Dermoscopy of a skin lesion.
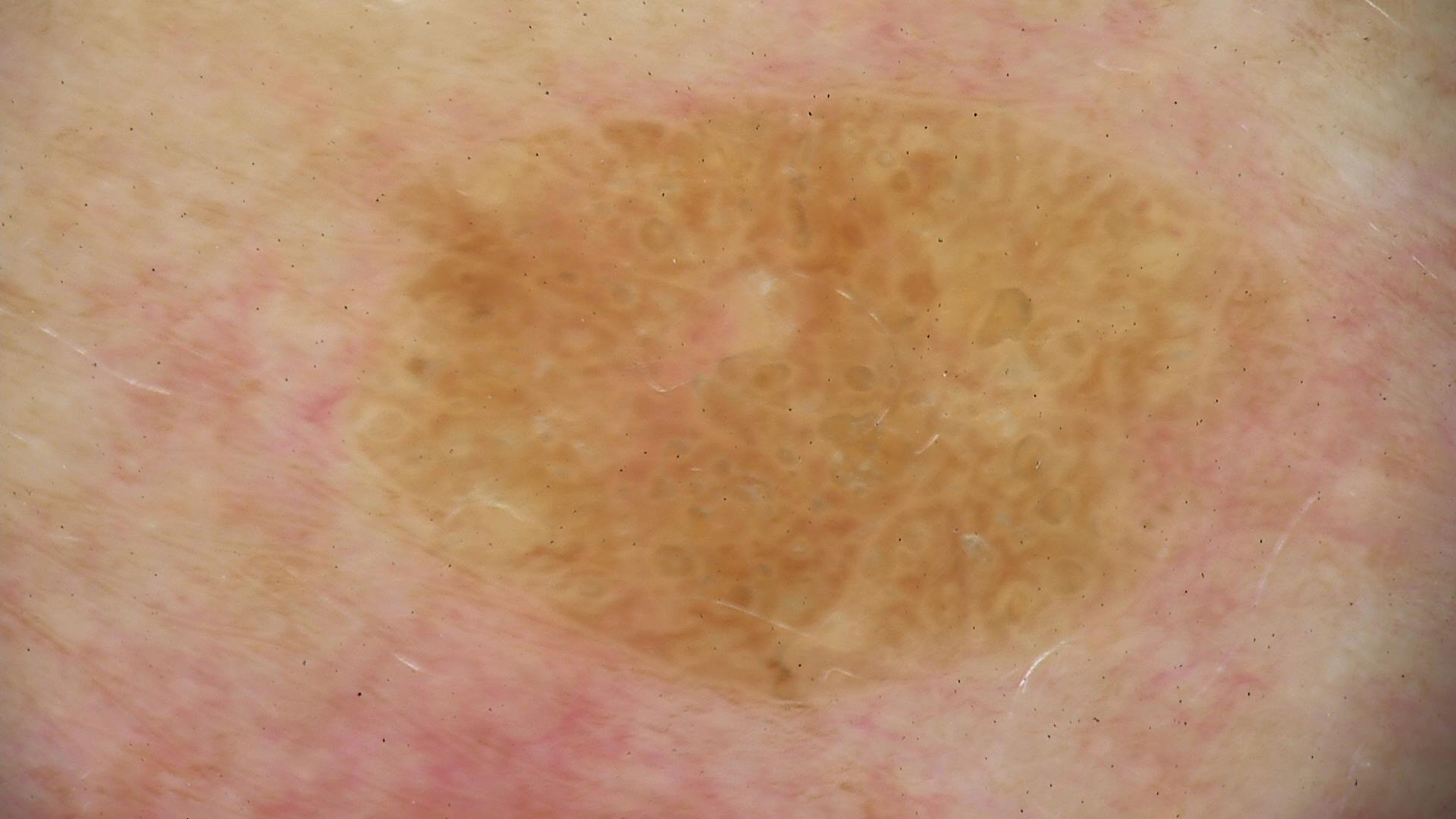  diagnosis:
    name: seborrheic keratosis
    code: sk
    malignancy: benign
    super_class: non-melanocytic
    confirmation: expert consensus